Texture is reported as rough or flaky. The photo was captured at an angle. The lesion involves the head or neck and leg. Lay graders estimated 3 on the Monk Skin Tone. The contributor is female: 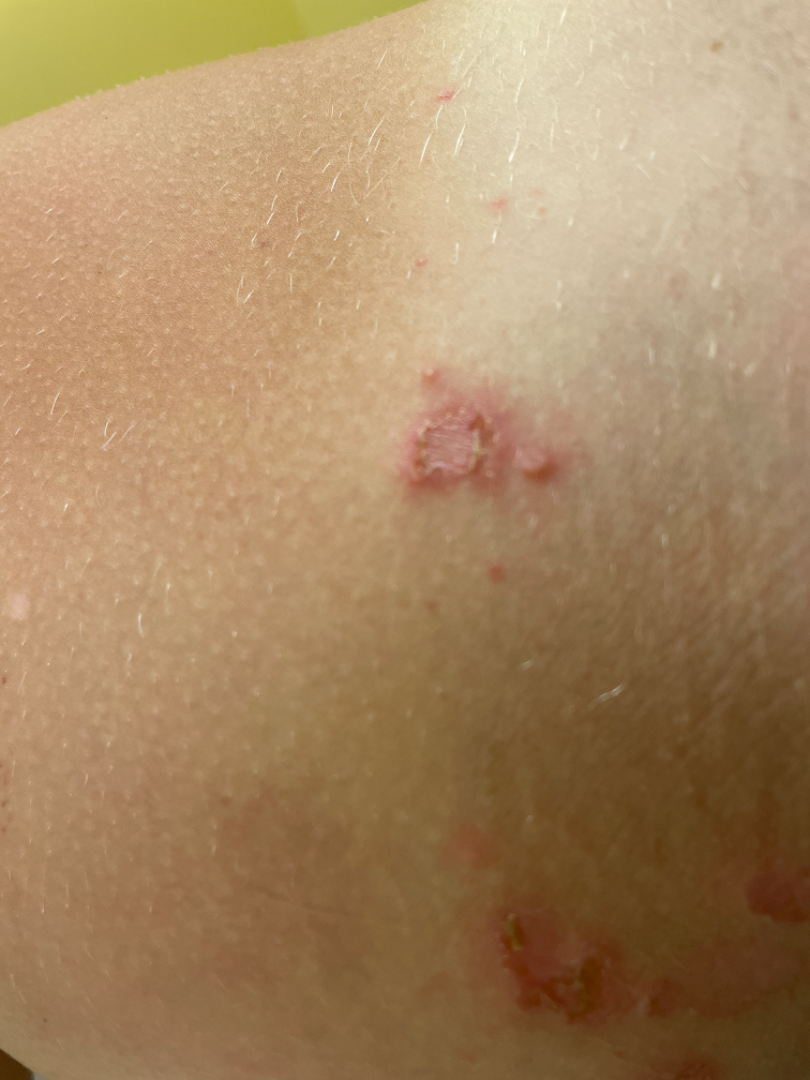assessment — could not be assessed